A dermoscopic image of a skin lesion.
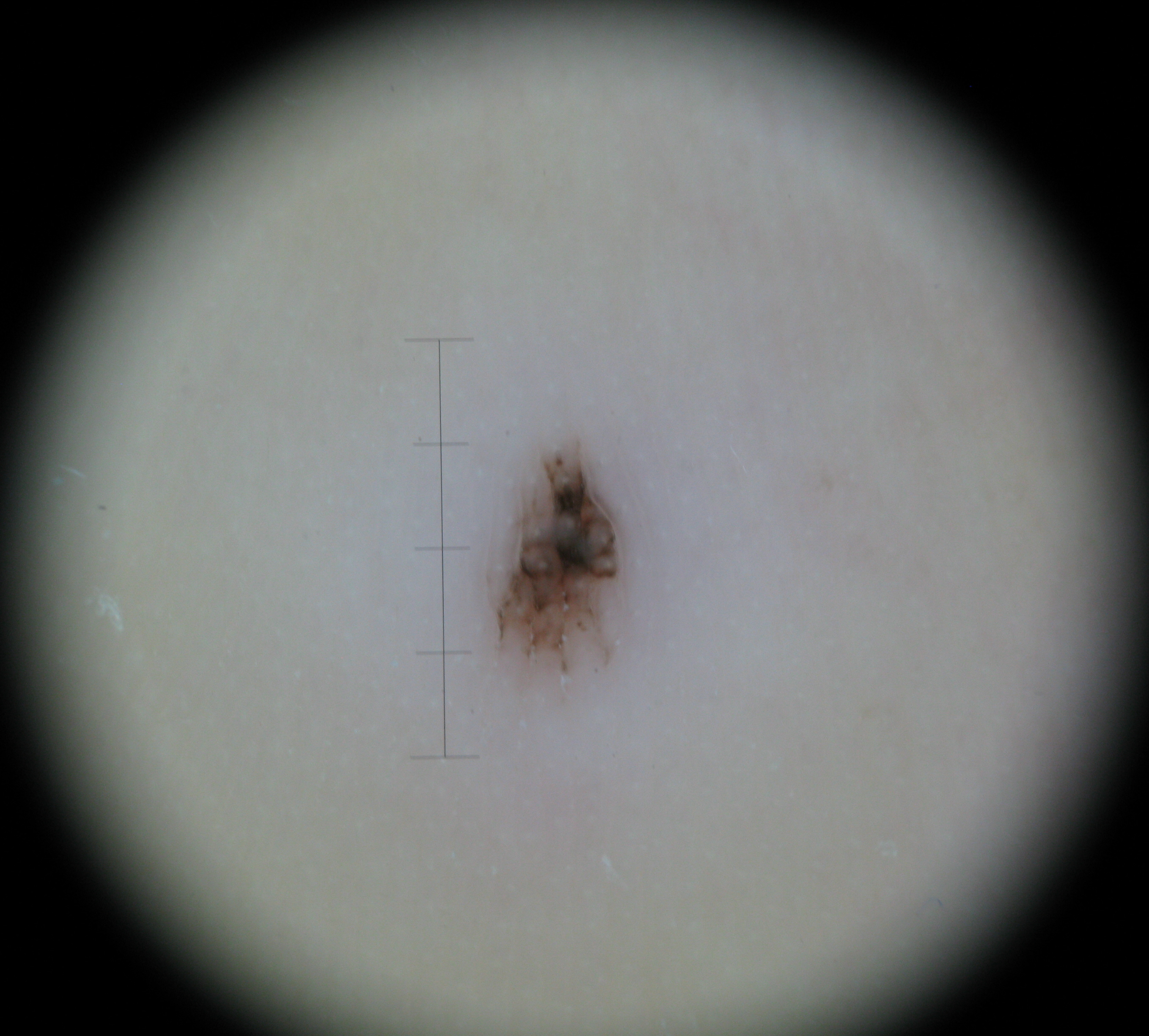| key | value |
|---|---|
| subtype | banal |
| class | acral compound nevus (expert consensus) |